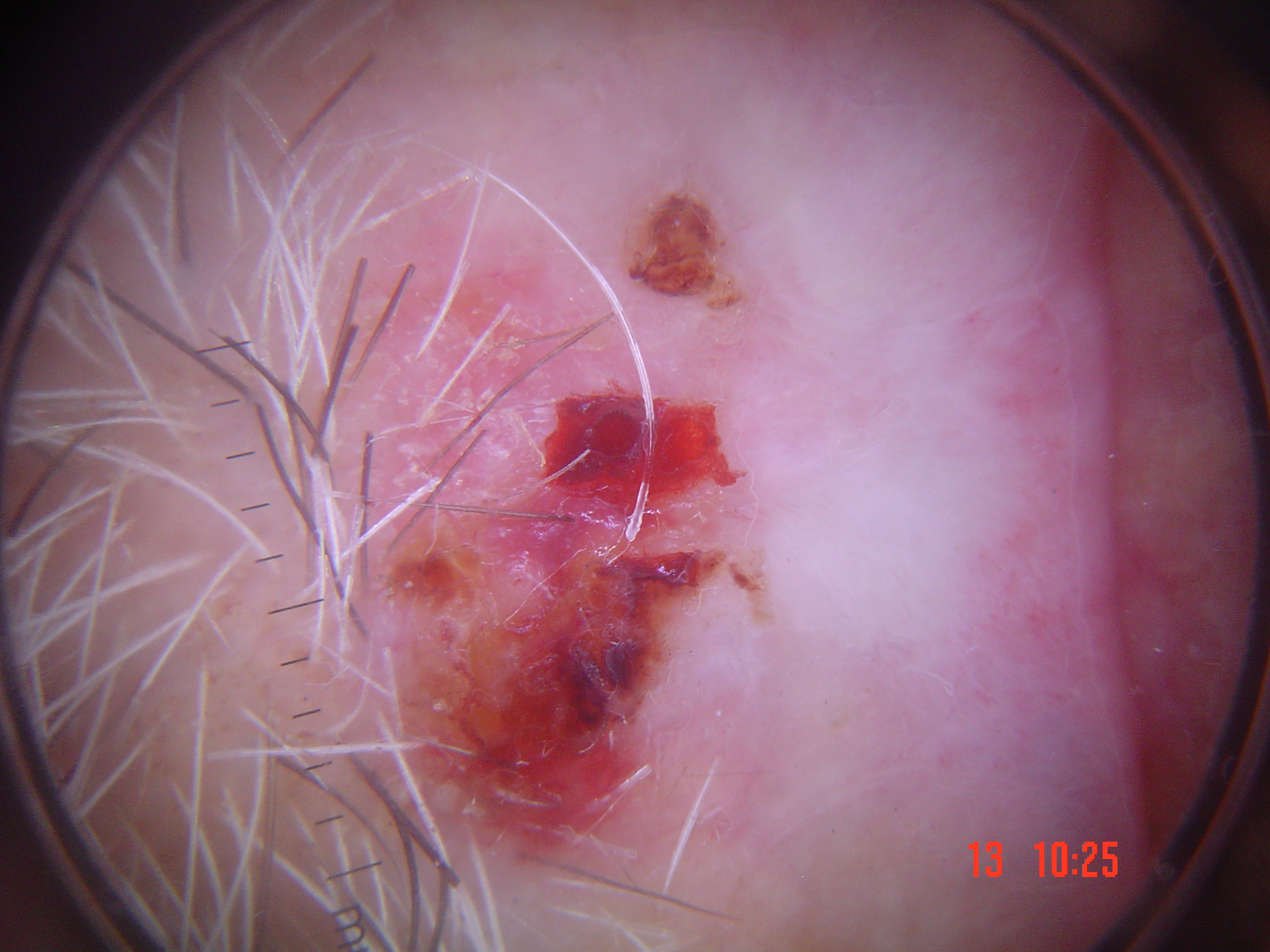The architecture is that of a keratinocytic lesion.
Confirmed on histopathology as a squamous cell carcinoma.